Close-up view, the contributor reports the condition has been present for about one day, self-categorized by the patient as a rash, symptoms reported: bothersome appearance:
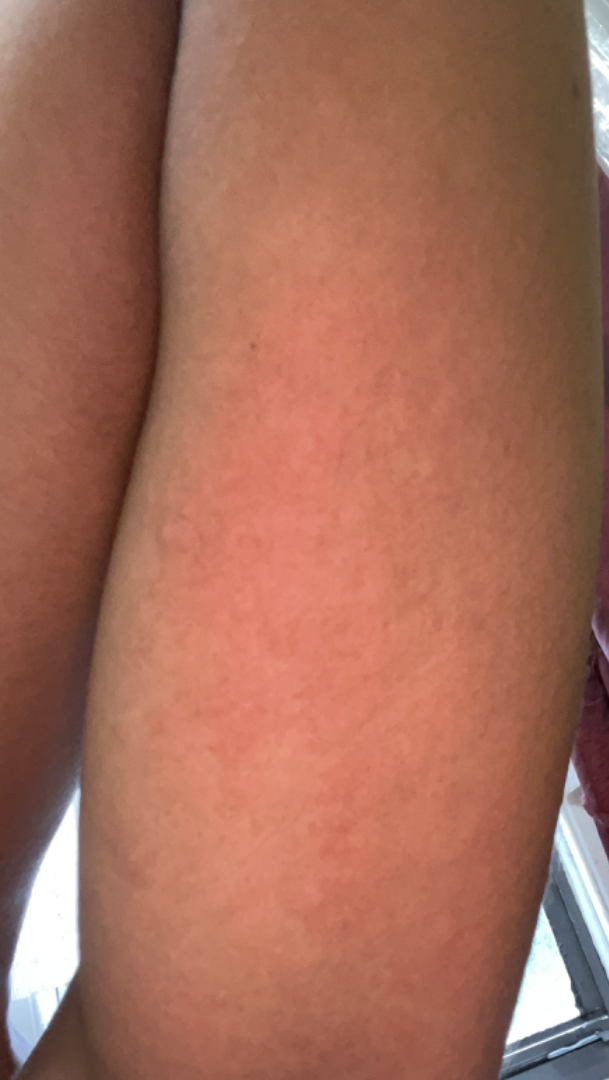Findings: The skin condition could not be confidently assessed from this image.